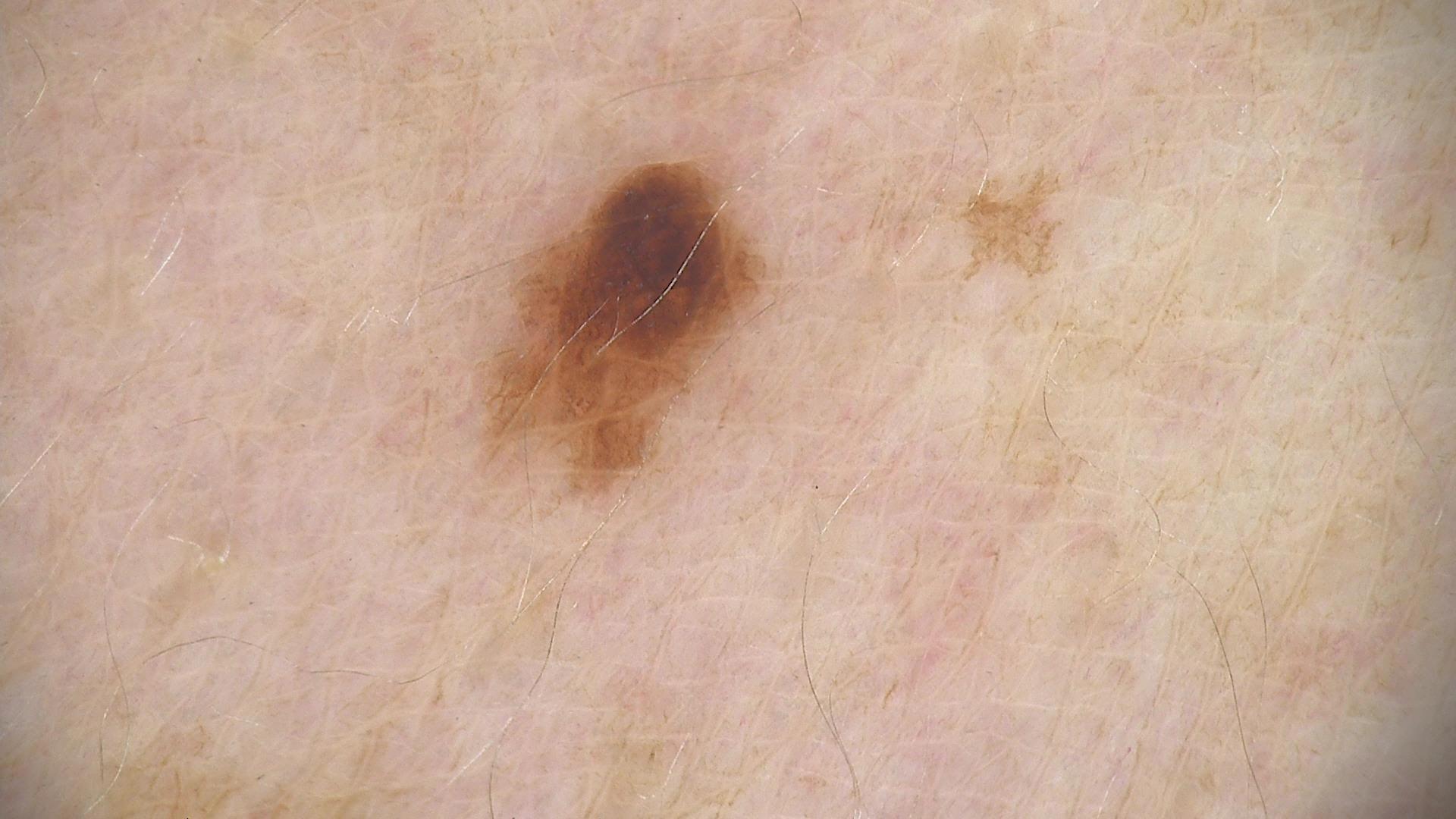{
  "image": "dermoscopy",
  "diagnosis": {
    "name": "dysplastic junctional nevus",
    "code": "jd",
    "malignancy": "benign",
    "super_class": "melanocytic",
    "confirmation": "expert consensus"
  }
}